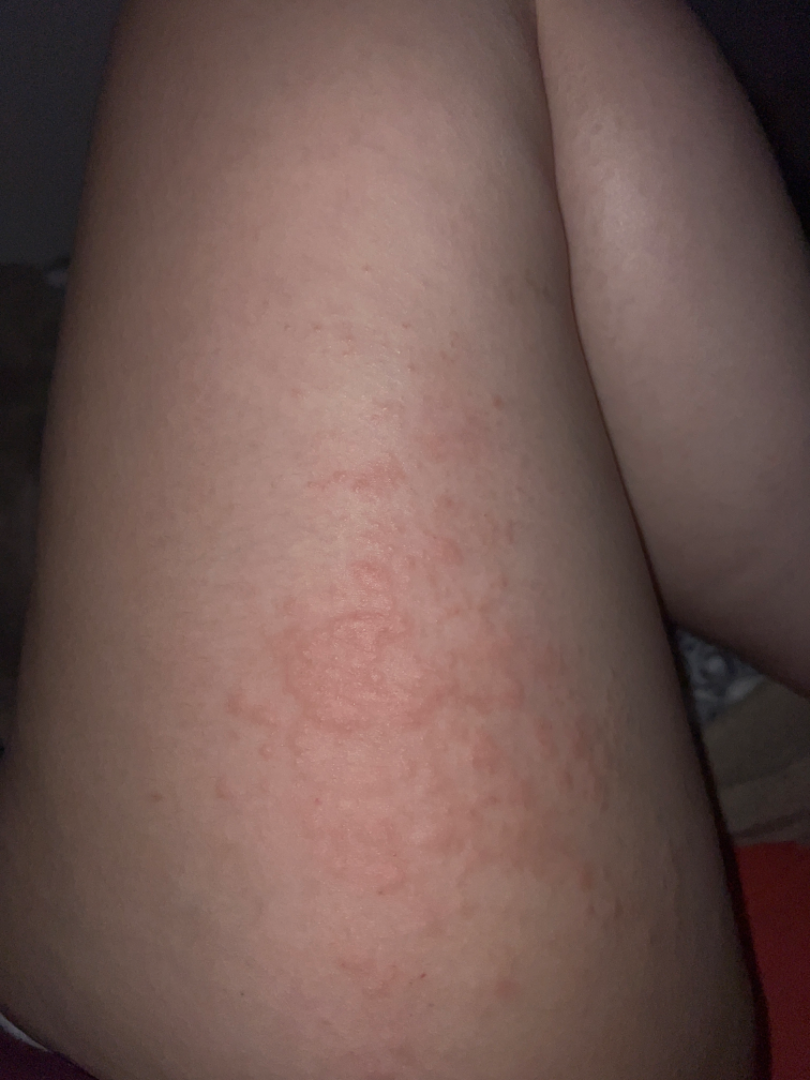Notes:
– location — leg
– duration — less than one week
– view — at an angle
– lesion texture — raised or bumpy
– lesion symptoms — itching, bothersome appearance and enlargement
– contributor — female, age 18–29
– self-categorized as — a rash
– differential — most consistent with Acute dermatitis, NOS